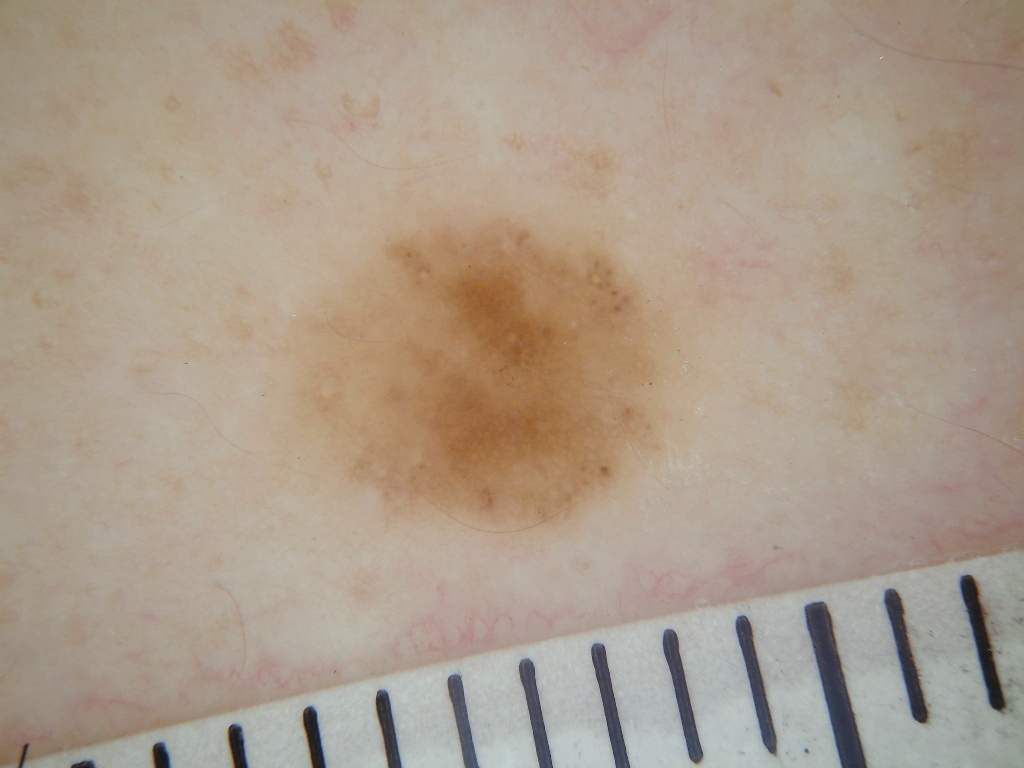patient = male, in their mid- to late 20s | modality = dermoscopic image | lesion location = box(278, 204, 683, 533) | dermoscopic pattern = pigment network; absent: globules, streaks, negative network, and milia-like cysts | assessment = a melanocytic nevus, a benign skin lesion.